The patient describes having numerous moles. A female patient 26 years of age. The patient says their skin reddens with sun exposure. A dermatoscopic image of a skin lesion.
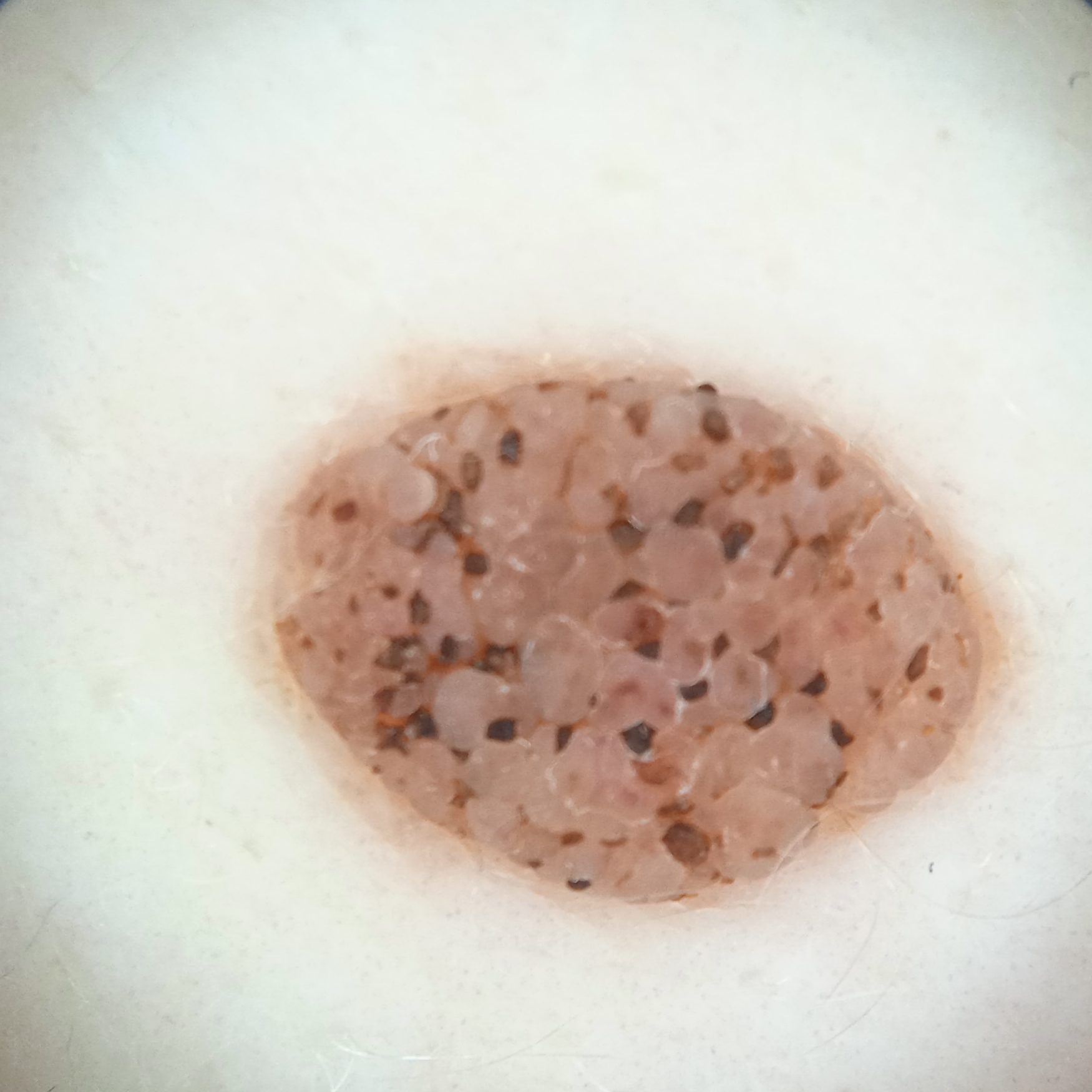  diagnosis:
    name: seborrheic keratosis
    malignancy: benign